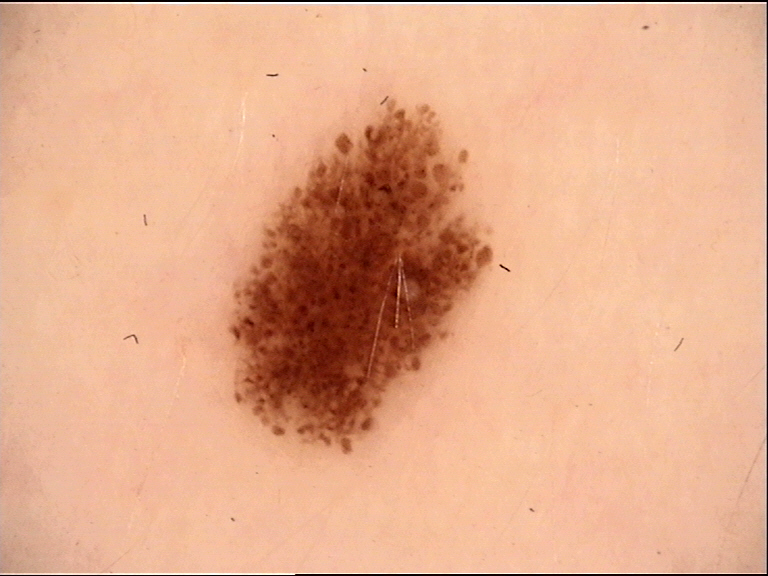Labeled as a dysplastic junctional nevus.